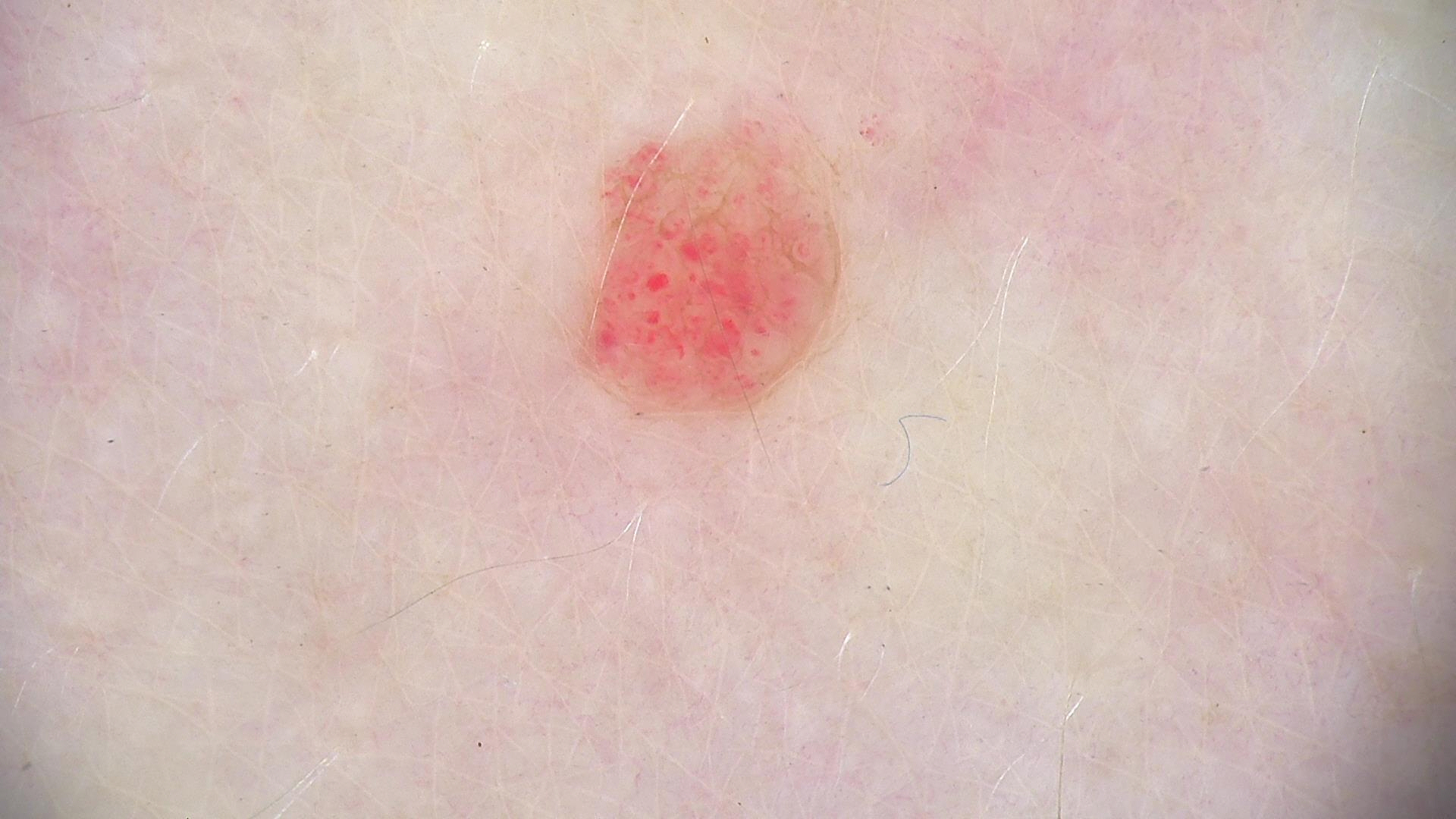Findings: A skin lesion imaged with a dermatoscope. Impression: Classified as a vascular lesion — a hemangioma.